Reported duration is one to four weeks · the patient reported no systemic symptoms · the patient reports the lesion is flat · female patient, age 18–29 · the lesion is associated with itching and bothersome appearance · the affected area is the leg · the patient described the issue as a rash · the photograph was taken at an angle:
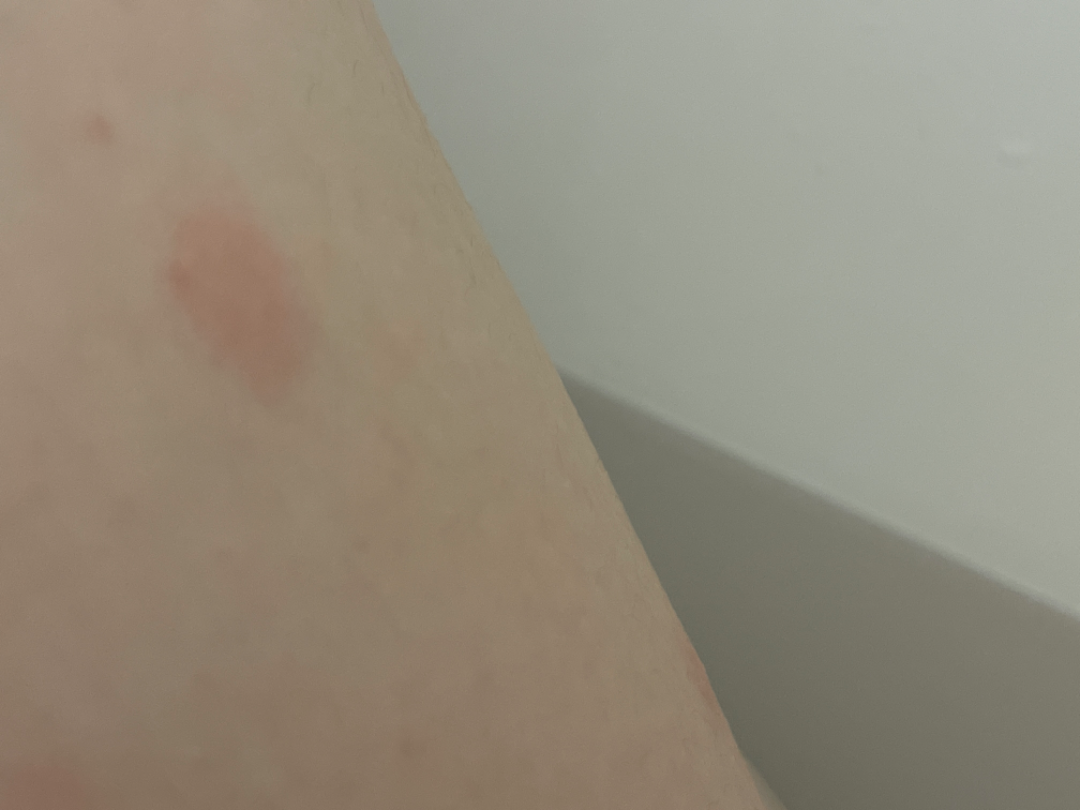assessment = Sweet syndrome (possible); Insect Bite (possible); Eczema (possible).